This image was taken at a distance:
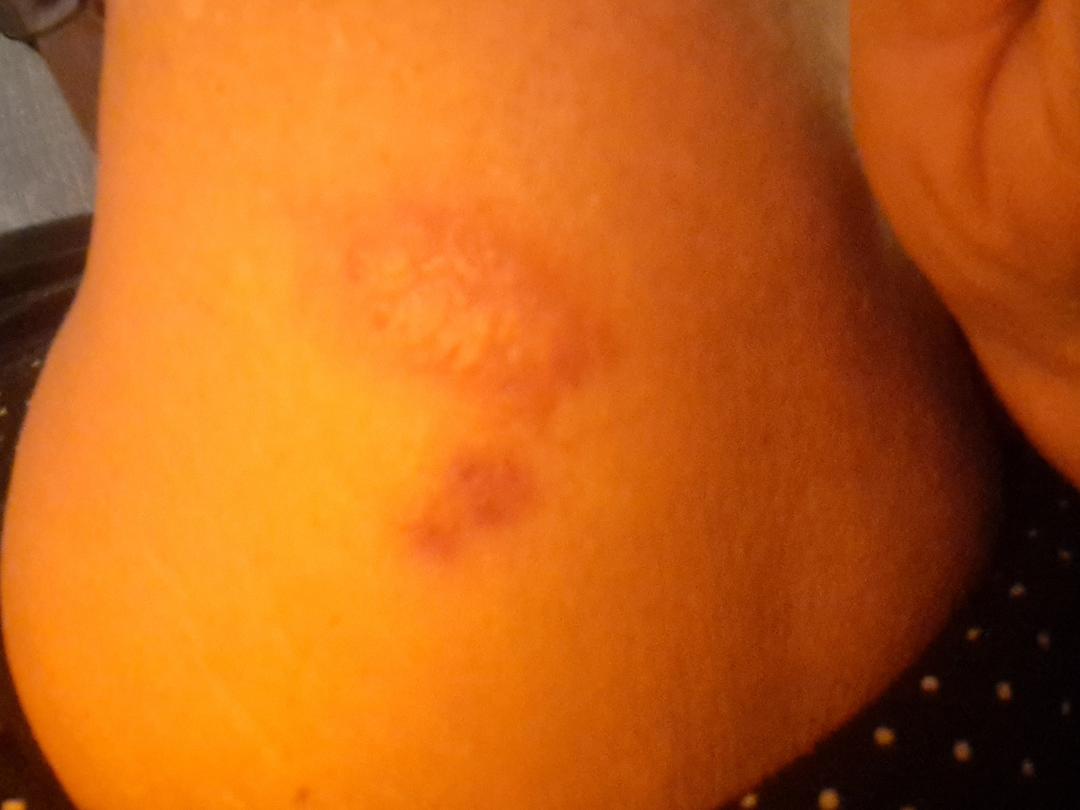The image was not sufficient for the reviewer to characterize the skin condition.